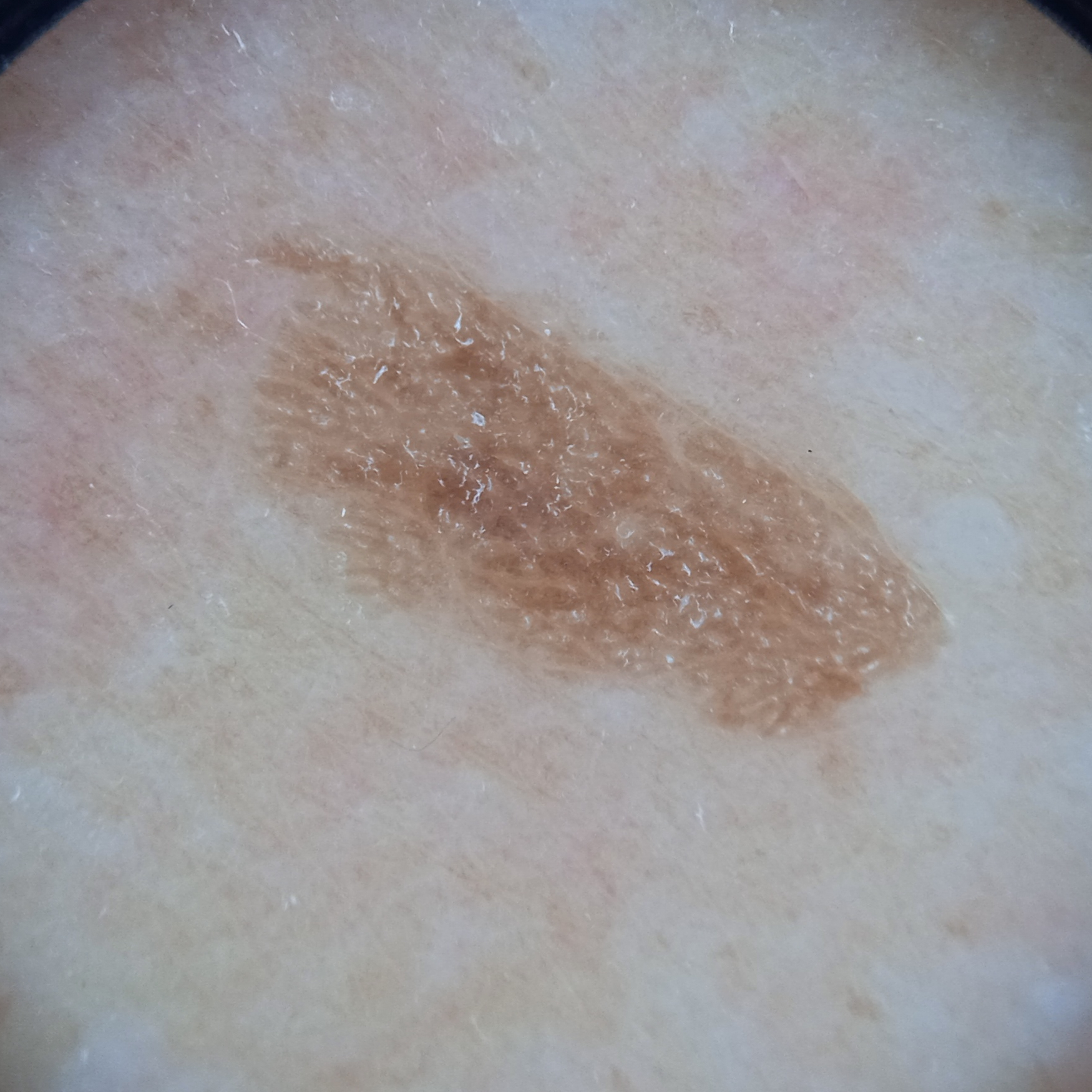{"patient": {"age": 75, "sex": "female"}, "sun_reaction": "skin tans without first burning", "risk_factors": {"positive": ["a personal history of skin cancer", "a personal history of cancer"]}, "referral": "research study (no referral diagnosis)", "image": "dermoscopy", "mole_burden": "a moderate number of melanocytic nevi", "lesion_location": "the back", "lesion_size": {"diameter_mm": 8.4}, "diagnosis": {"name": "seborrheic keratosis", "malignancy": "benign"}}